The photograph is a close-up of the affected area:
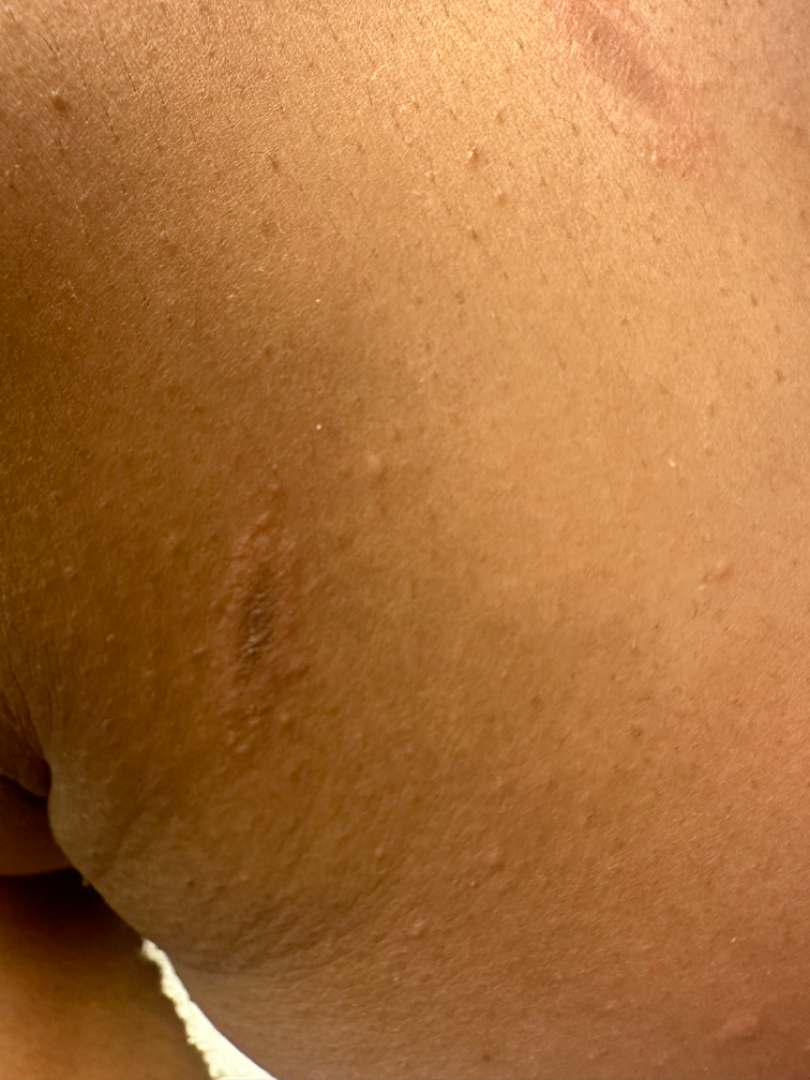texture: rough or flaky
symptoms:
  - bothersome appearance
  - darkening
duration: about one day
differential:
  leading:
    - Erythema multiforme